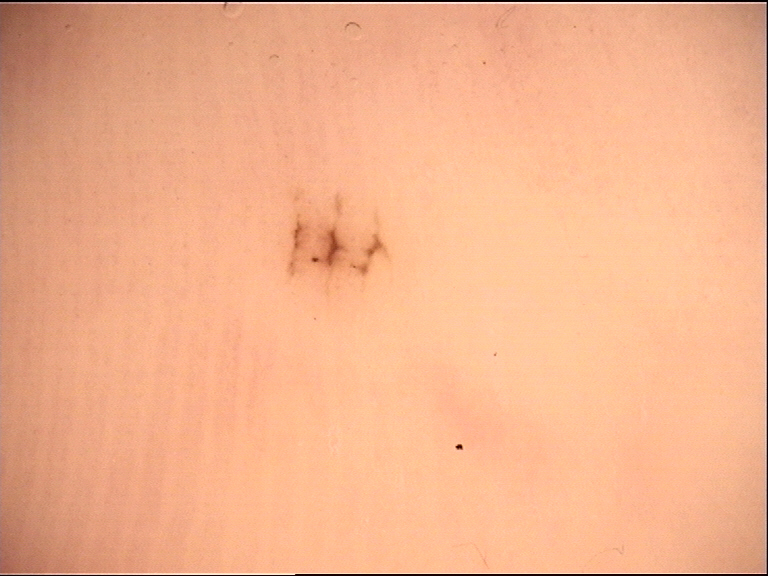Summary:
A dermoscopic close-up of a skin lesion.
Impression:
Consistent with an acral dysplastic junctional nevus.